The arm, leg and back of the hand are involved · the subject is 18–29, female · the photograph is a close-up of the affected area:
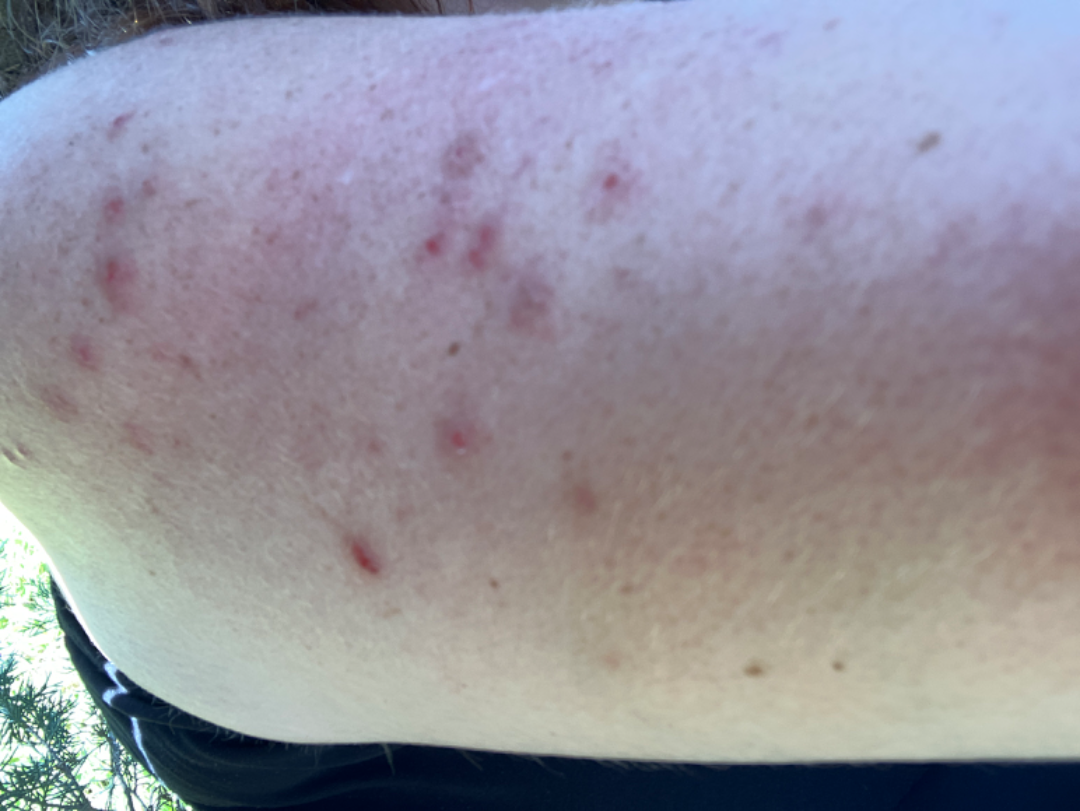A single dermatologist reviewed the case: the differential is split between Prurigo, Folliculitis and Insect Bite.